A male patient, aged 63 to 67 · a dermoscopic image of a skin lesion:
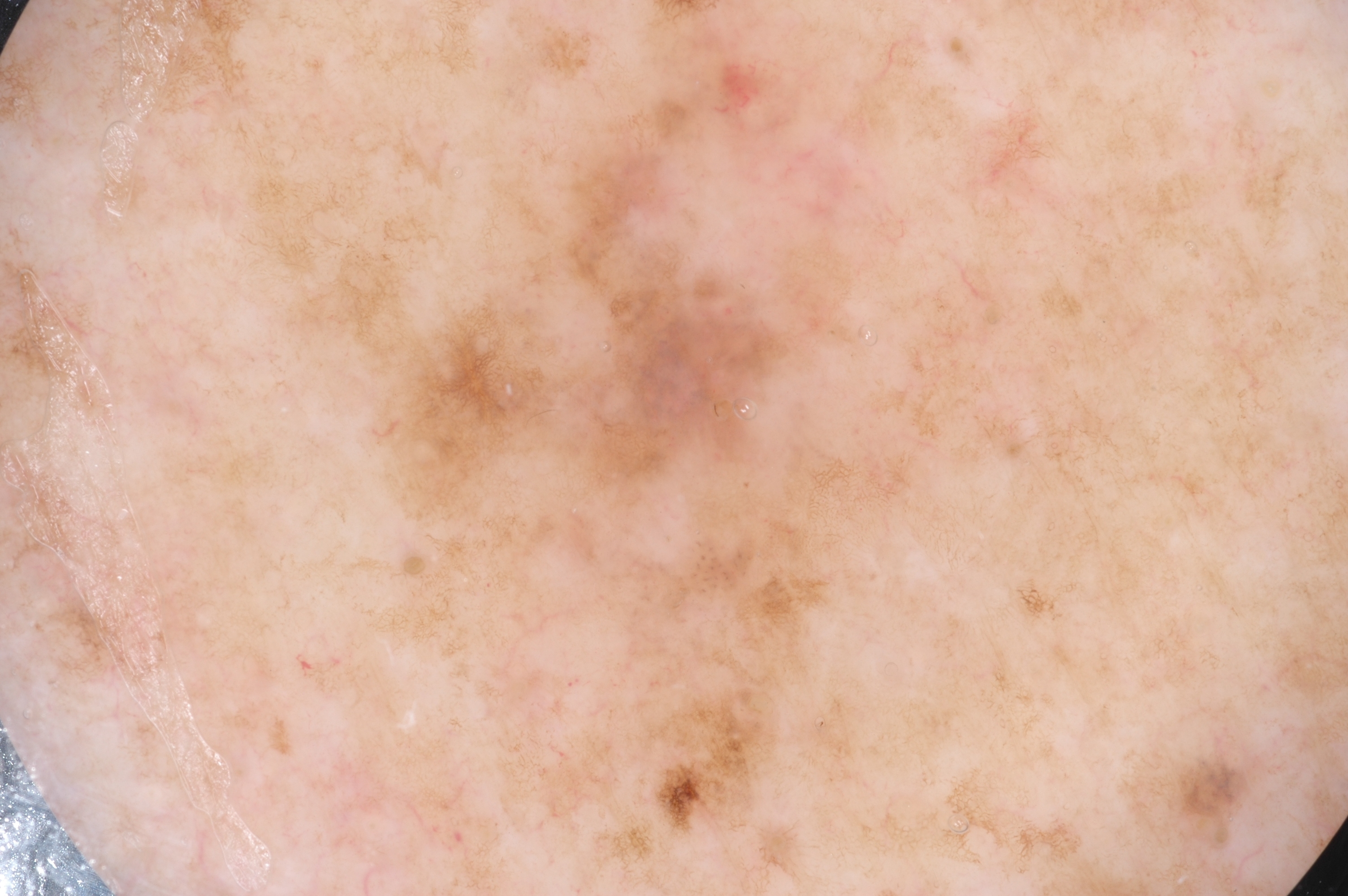dermoscopic pattern=pigment network; lesion extent=~27% of the field; lesion bbox=[365, 47, 1000, 855]; diagnostic label=a melanoma, a skin cancer.